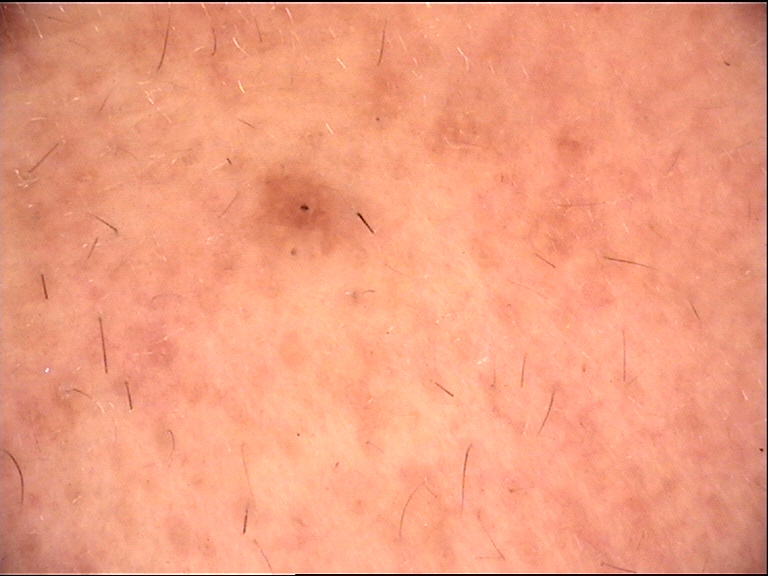Conclusion:
Labeled as a banal lesion — a Miescher nevus.